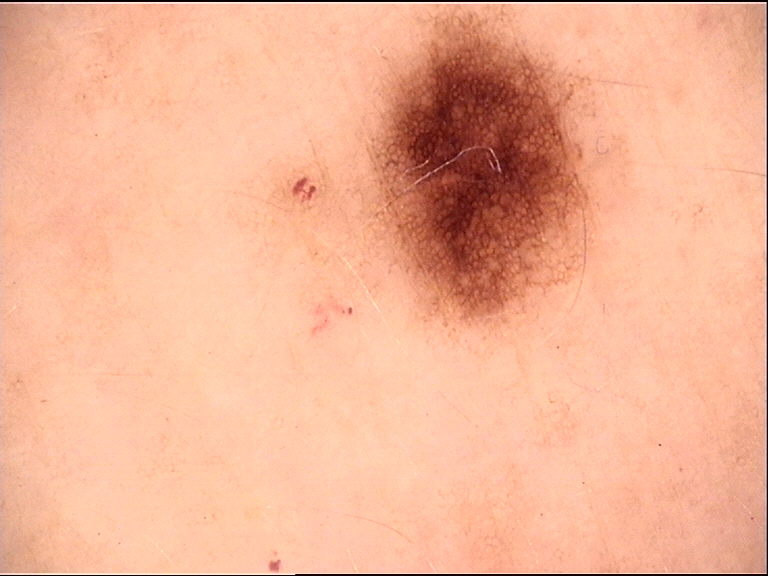Findings:
– assessment — dysplastic junctional nevus (expert consensus)